This image was taken at a distance · the patient is 50–59, female — 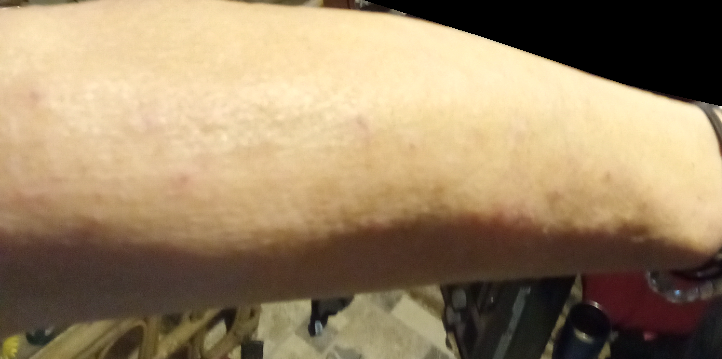Q: What is the dermatologist's impression?
A: the impression on review was Eczema